The patient reports a family history of skin cancer and a history of sunbed use; a female subject age 48; the patient says their skin reddens painfully with sun exposure:
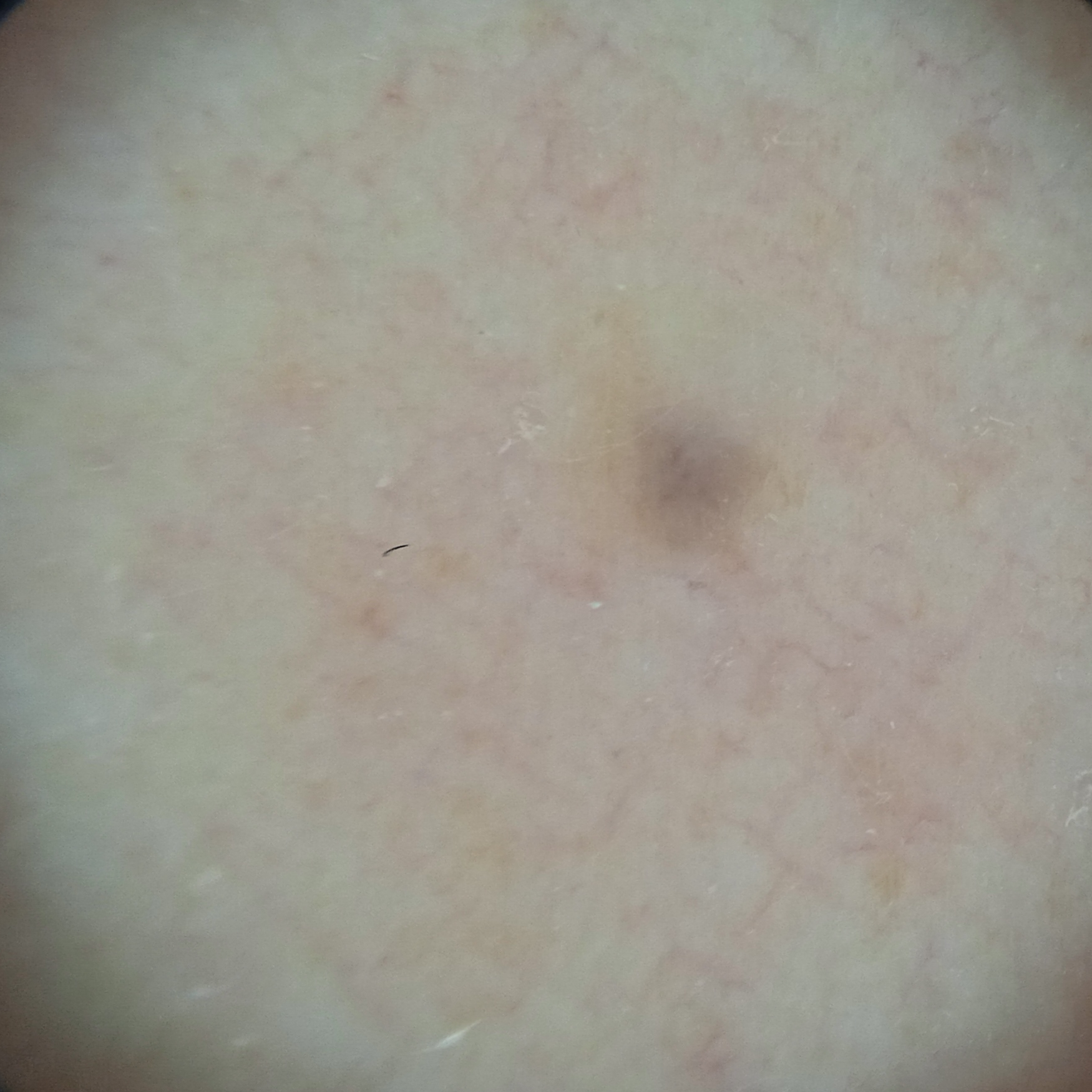The lesion involves an arm. The lesion measures approximately 1.8 mm. The diagnostic impression was a melanocytic nevus.